The photo was captured at an angle. Fitzpatrick phototype IV.
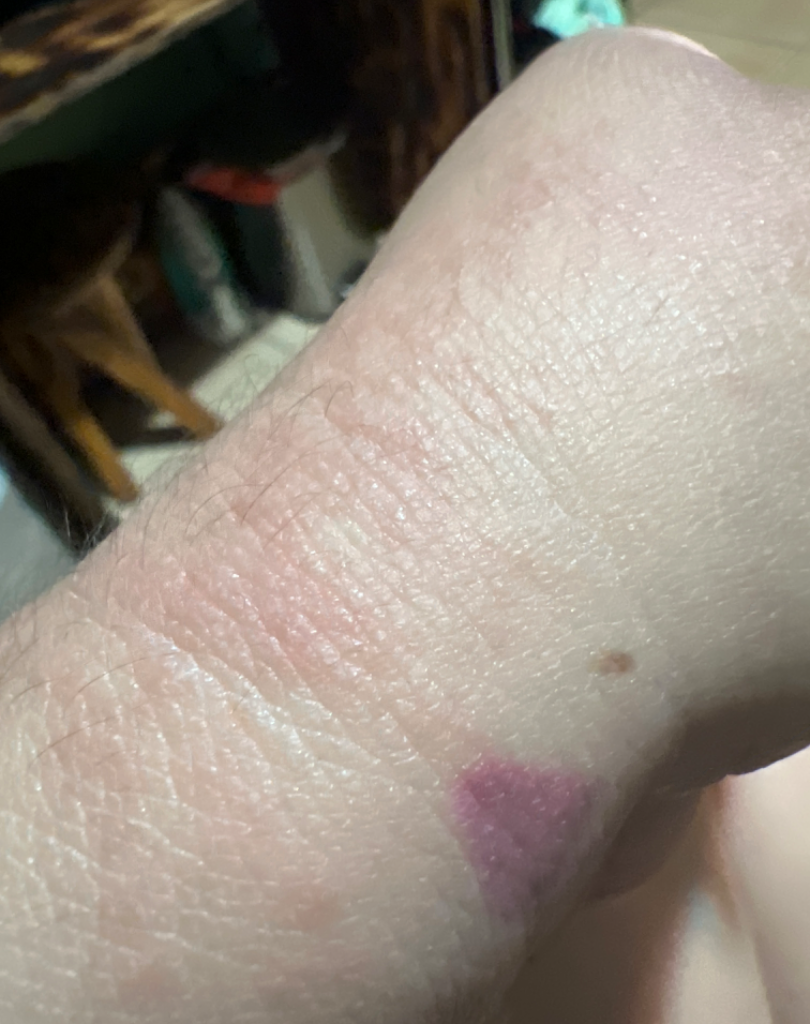On dermatologist assessment of the image: the differential includes Scabies and Hypersensitivity, with no clear leading consideration.